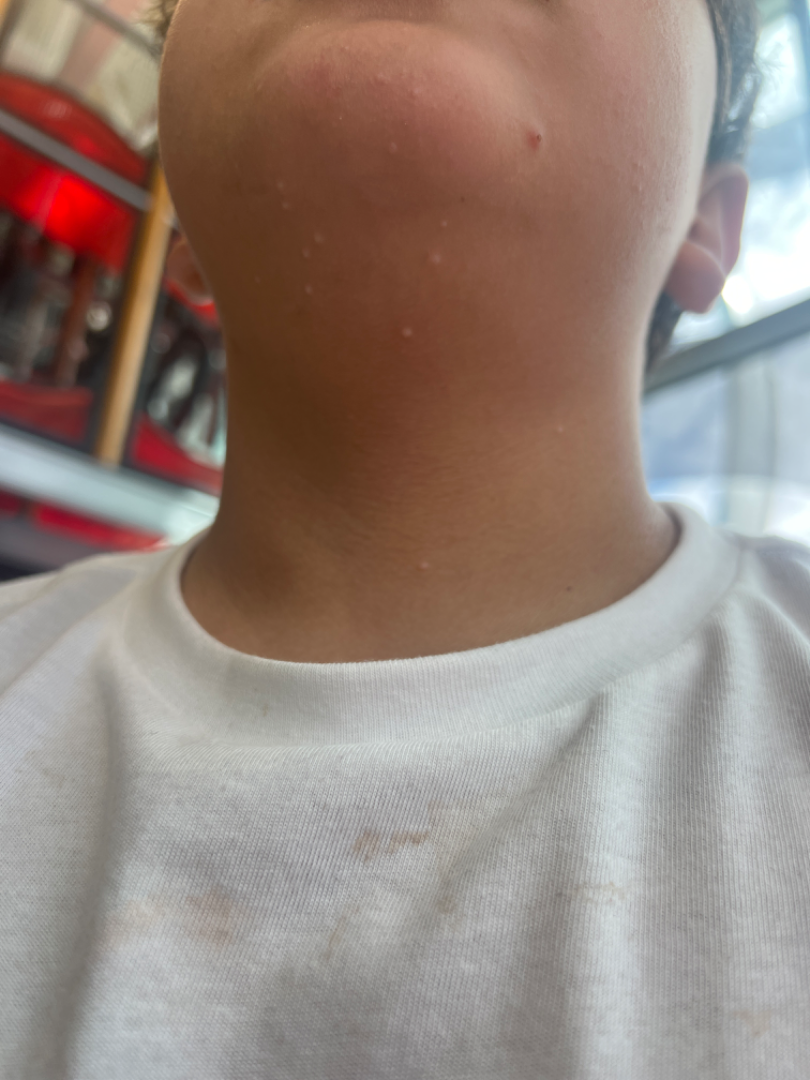The case was difficult to assess from the available photograph.